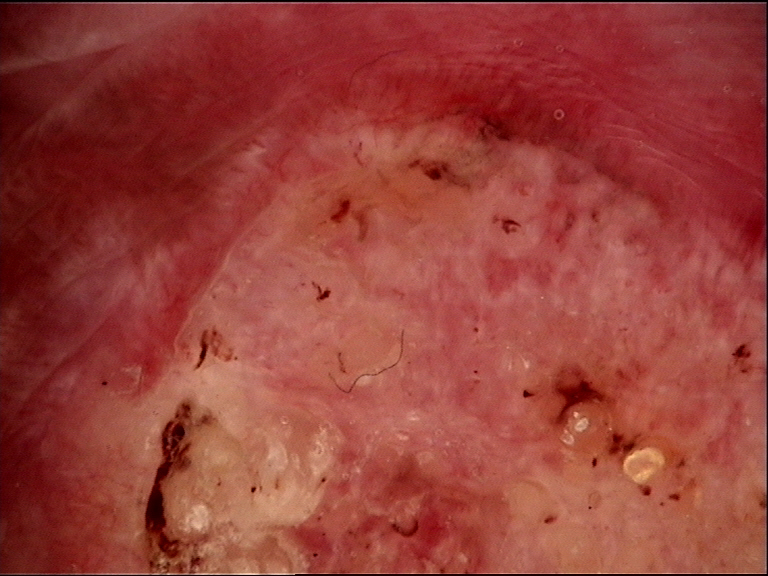lesion type: keratinocytic, class: squamous cell carcinoma (biopsy-proven).